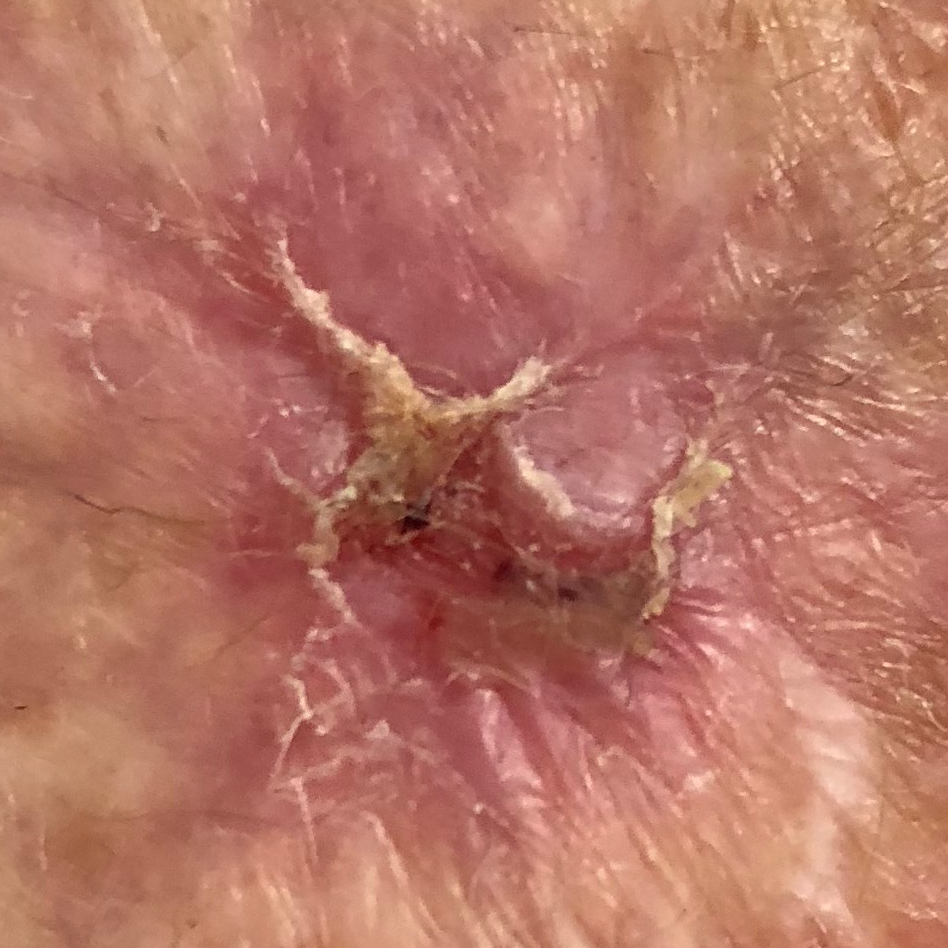Patient and lesion: Skin type II. The chart records prior malignancy (patient or family) and no tobacco use. A female patient aged 76. A clinical photograph showing a skin lesion. Per patient report, the lesion is elevated, has bled, and itches. Conclusion: The biopsy diagnosis was a squamous cell carcinoma.